Lay graders estimated 3 on the Monk Skin Tone. A close-up photograph:
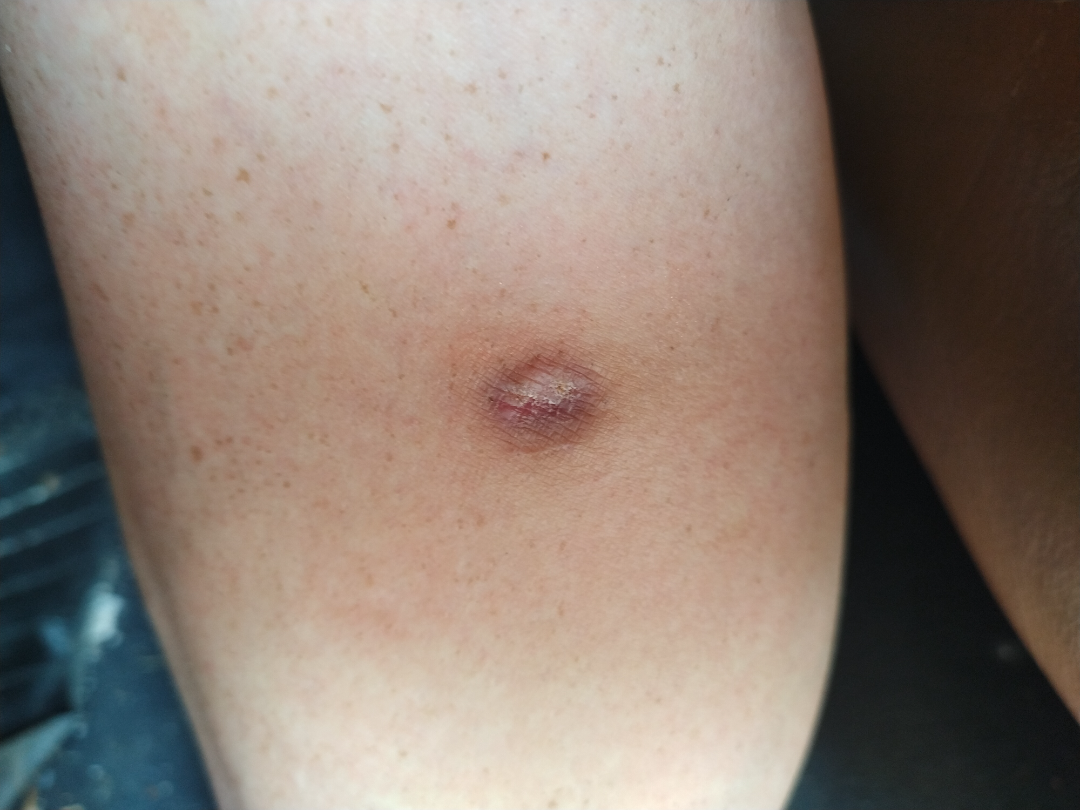<summary>
<differential>
  <tied_lead>Prurigo nodularis, SCC/SCCIS</tied_lead>
  <unlikely>Actinic Keratosis</unlikely>
</differential>
</summary>